A close-up photograph. The patient considered this a rash. The leg is involved. No relevant systemic symptoms. Present for less than one week. The contributor is a female aged 50–59: 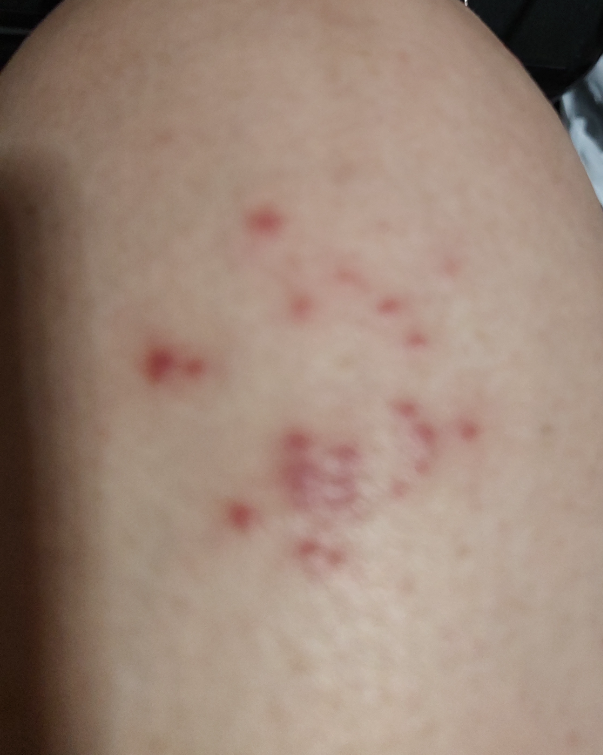The favored diagnosis is Herpes Zoster.